A patient in their late 40s: 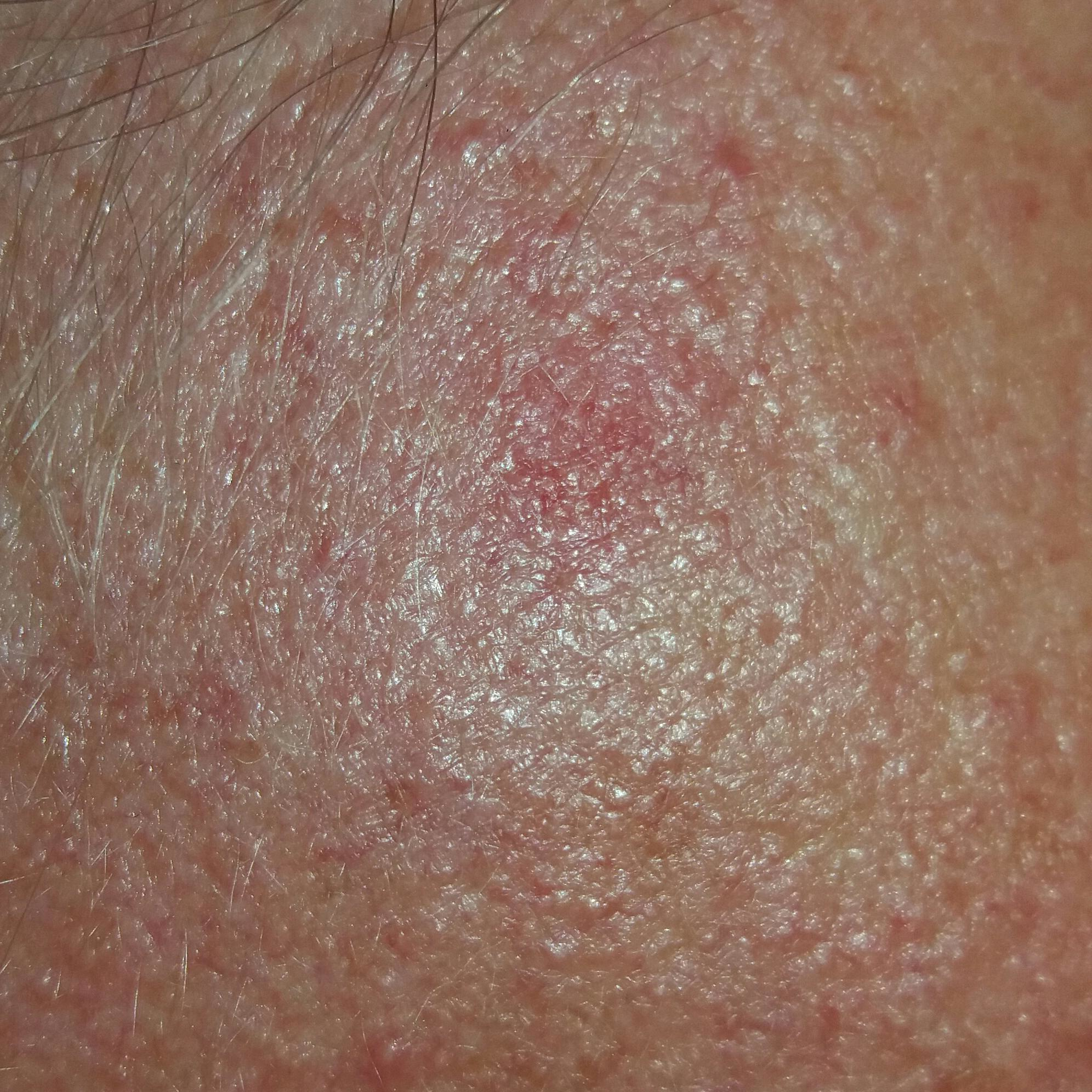| feature | finding |
|---|---|
| location | the face |
| patient-reported symptoms | itching / no pain, no bleeding |
| impression | actinic keratosis (clinical consensus) |